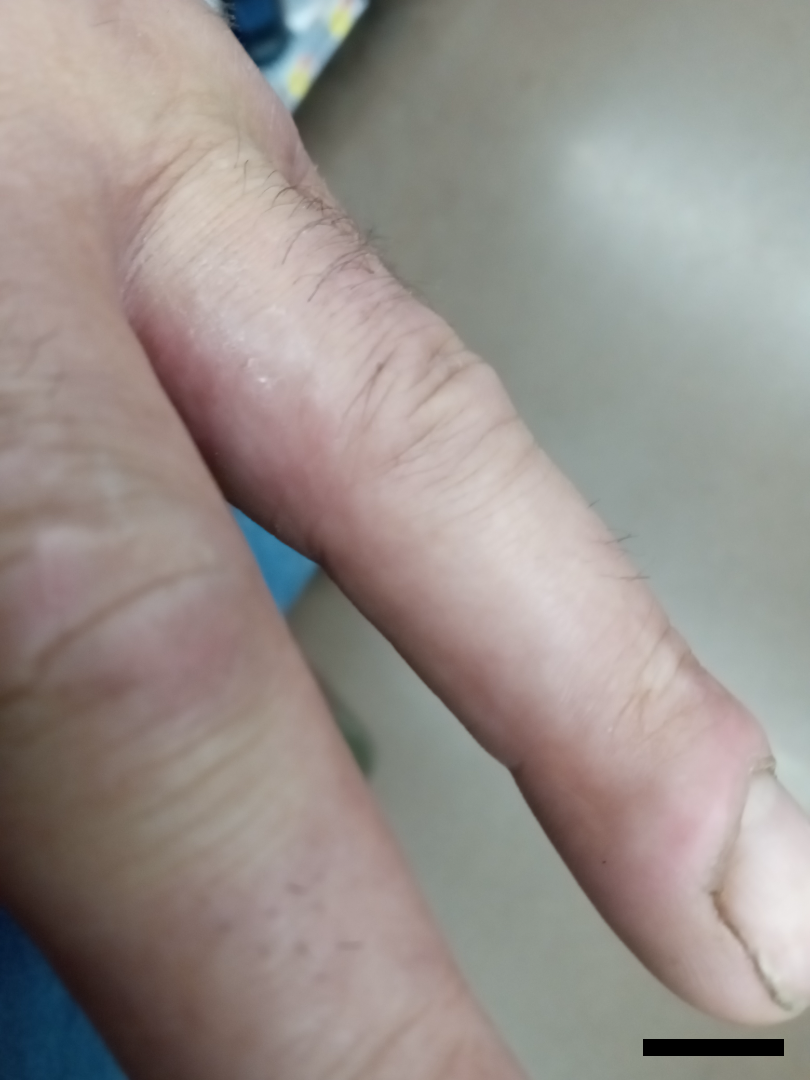The skin condition could not be confidently assessed from this image.